Located on the back of the torso. The contributor is a female aged 18–29. Close-up view: 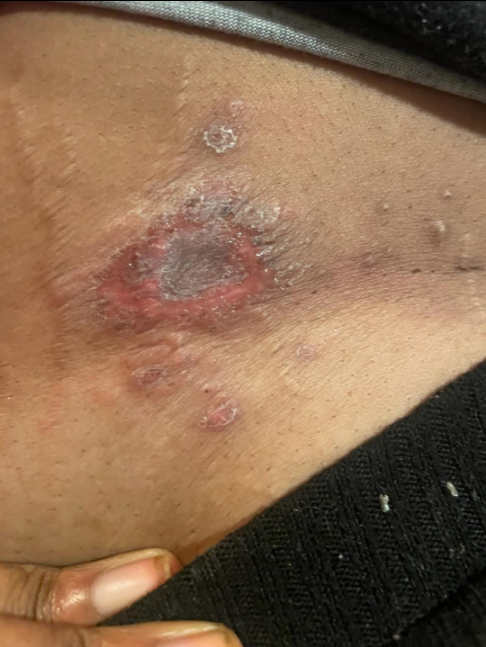On dermatologist assessment of the image: Cutaneous sarcoidosis and SCC/SCCIS were each considered, in no particular order.